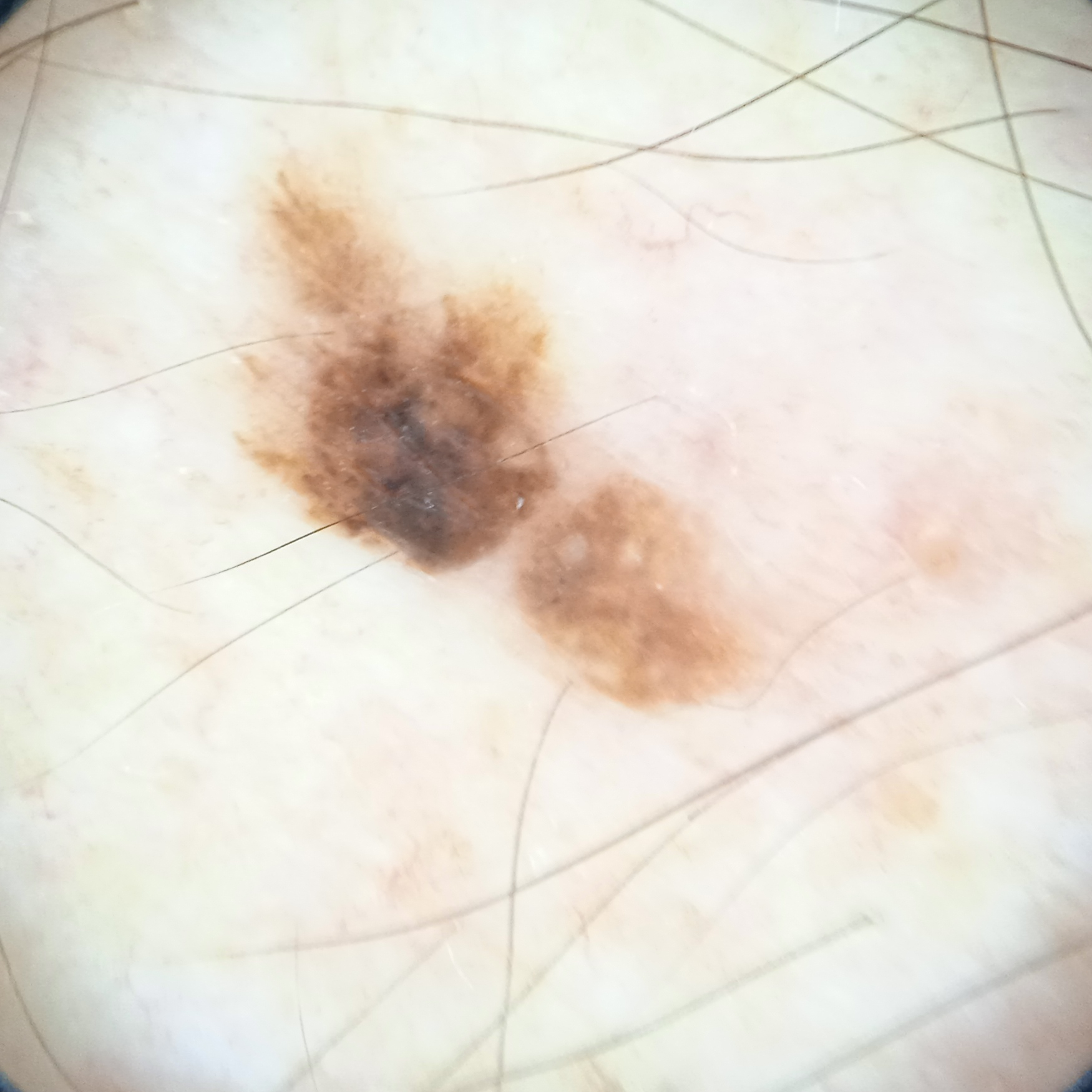imaging = dermoscopic image; clinical context = research study (no referral diagnosis); subject = male, 76 years of age; lesion size = 7.8 mm; assessment = seborrheic keratosis (dermatologist consensus).